A dermoscopy image of a single skin lesion.
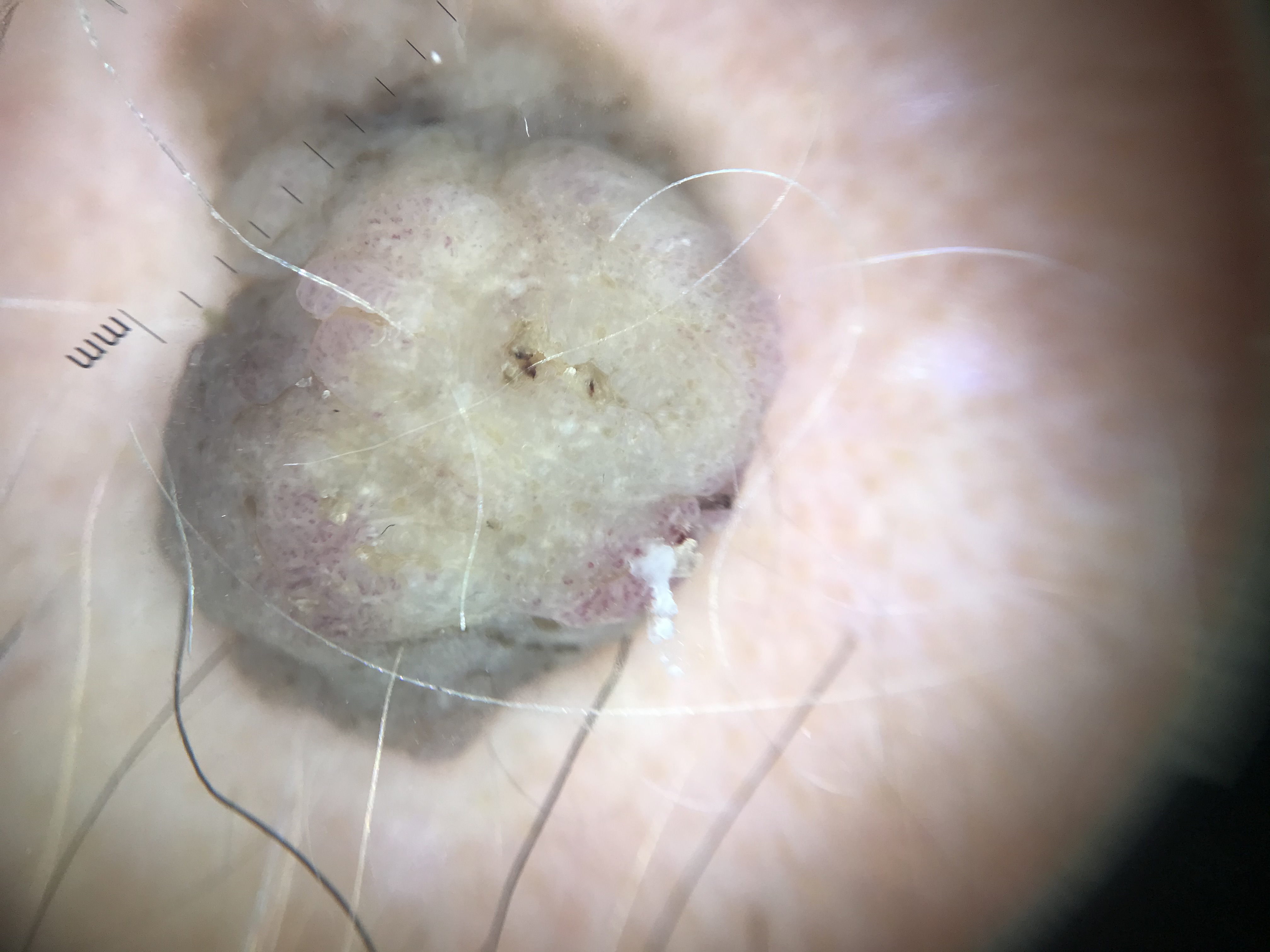Q: What was the diagnostic impression?
A: seborrheic keratosis (expert consensus)